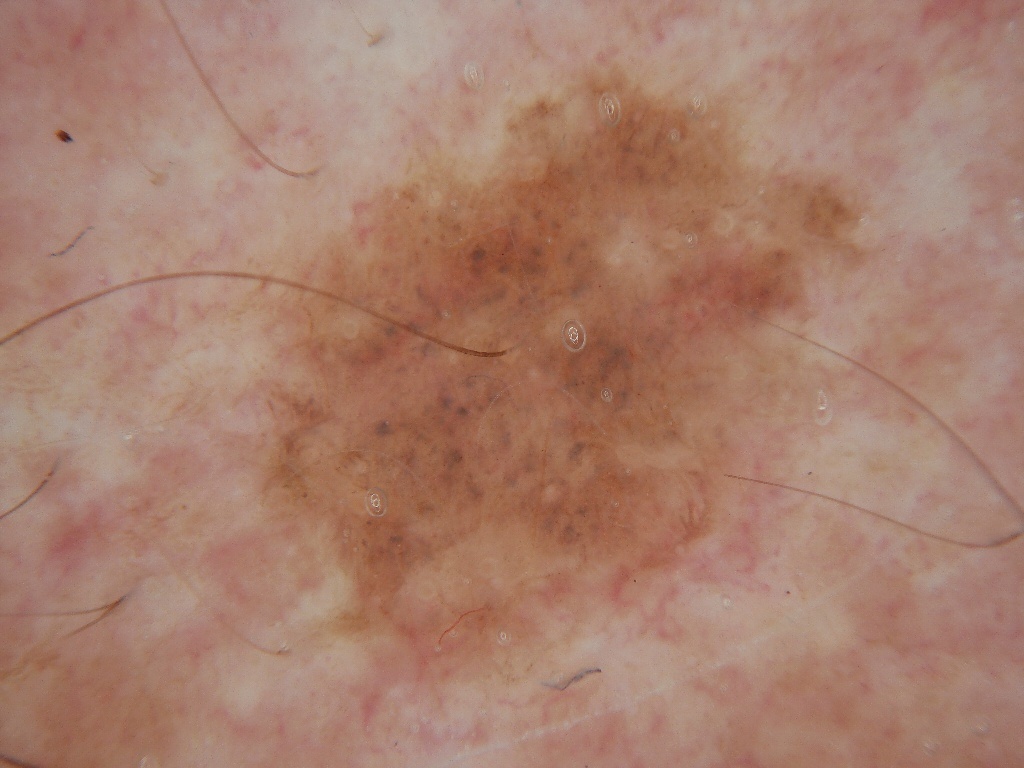A dermoscopic image of a skin lesion. With coordinates (x1, y1, x2, y2), the lesion is bounded by (210, 41, 891, 723). Clinically diagnosed as a benign lesion.